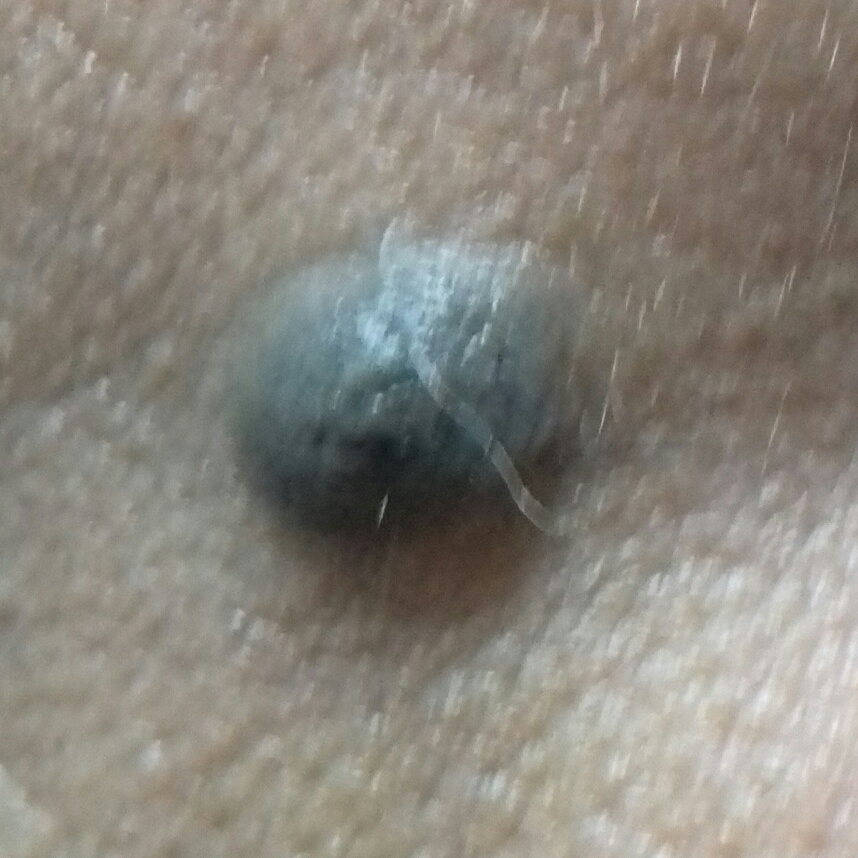Q: What symptoms does the patient report?
A: elevation, growth
Q: What is this lesion?
A: nevus (clinical consensus)